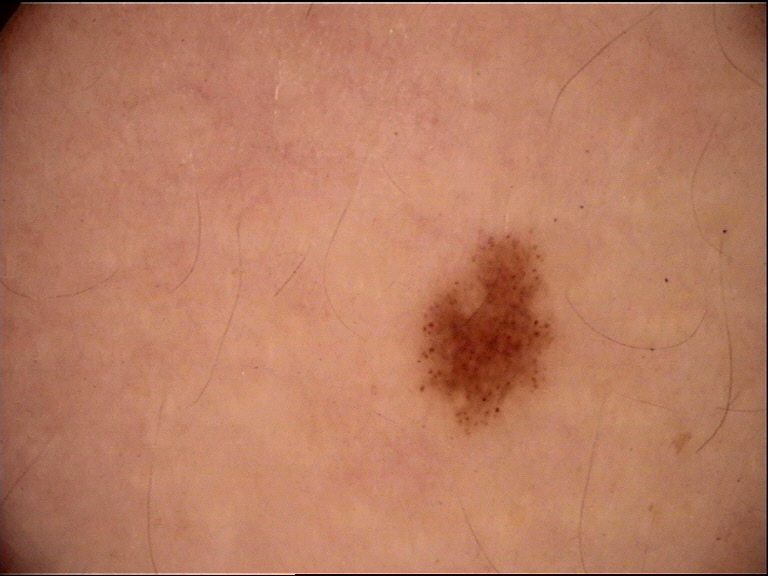{
  "diagnosis": {
    "name": "dysplastic junctional nevus",
    "code": "jd",
    "malignancy": "benign",
    "super_class": "melanocytic",
    "confirmation": "expert consensus"
  }
}